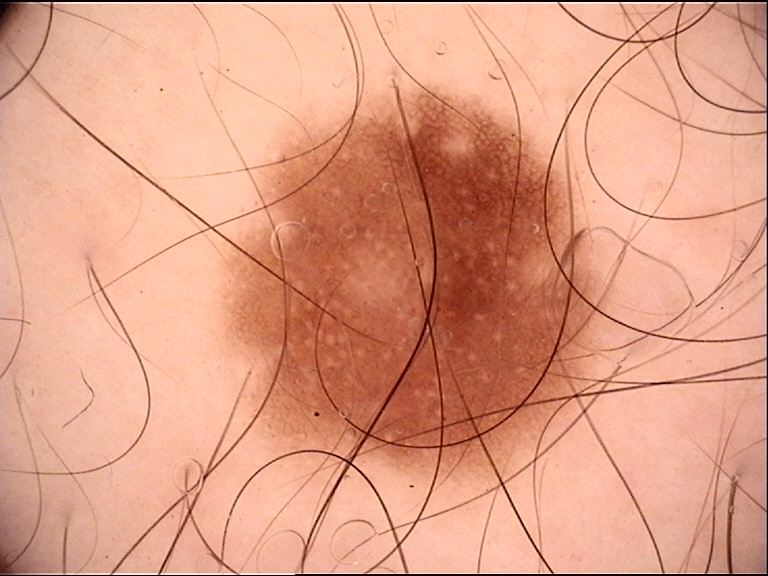Case:
A skin lesion imaged with a dermatoscope.
Impression:
Labeled as a dysplastic junctional nevus.